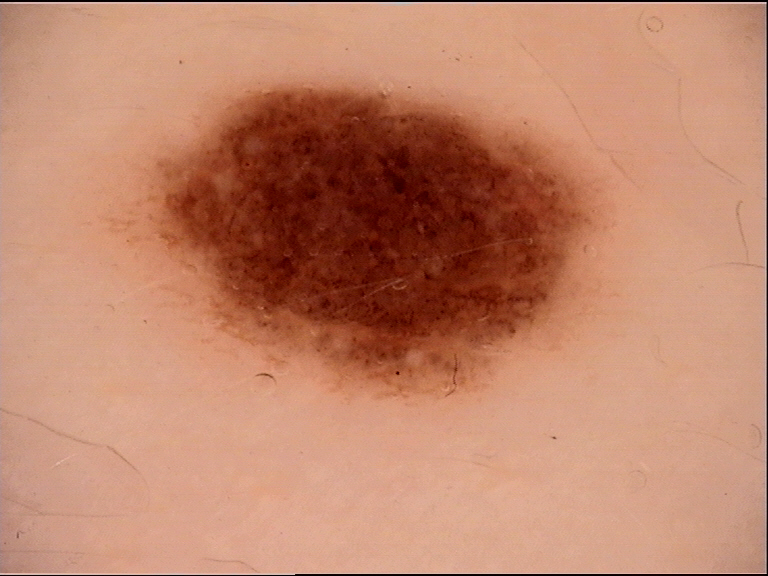Summary: The morphology is that of a banal lesion. Conclusion: Labeled as a compound nevus.